Dermoscopy of a skin lesion · a male subject roughly 75 years of age — 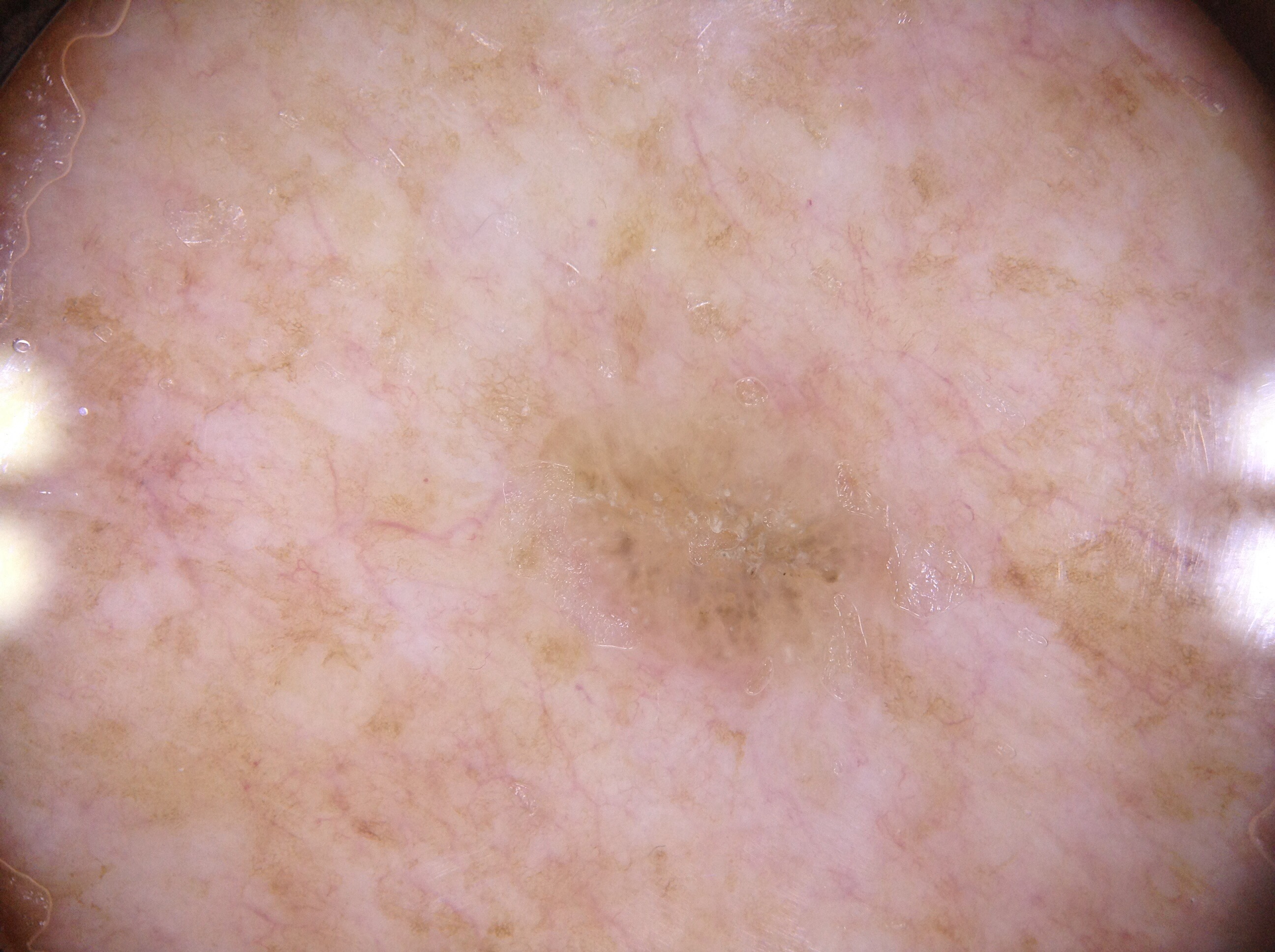{"lesion_location": {"bbox_xyxy": [526, 355, 914, 698]}, "dermoscopic_features": {"present": [], "absent": ["milia-like cysts", "negative network", "pigment network", "streaks"]}, "lesion_extent": "moderate", "diagnosis": {"name": "seborrheic keratosis", "malignancy": "benign", "lineage": "keratinocytic", "provenance": "clinical"}}